The patient is a male aged 30–39, the leg is involved, close-up view.
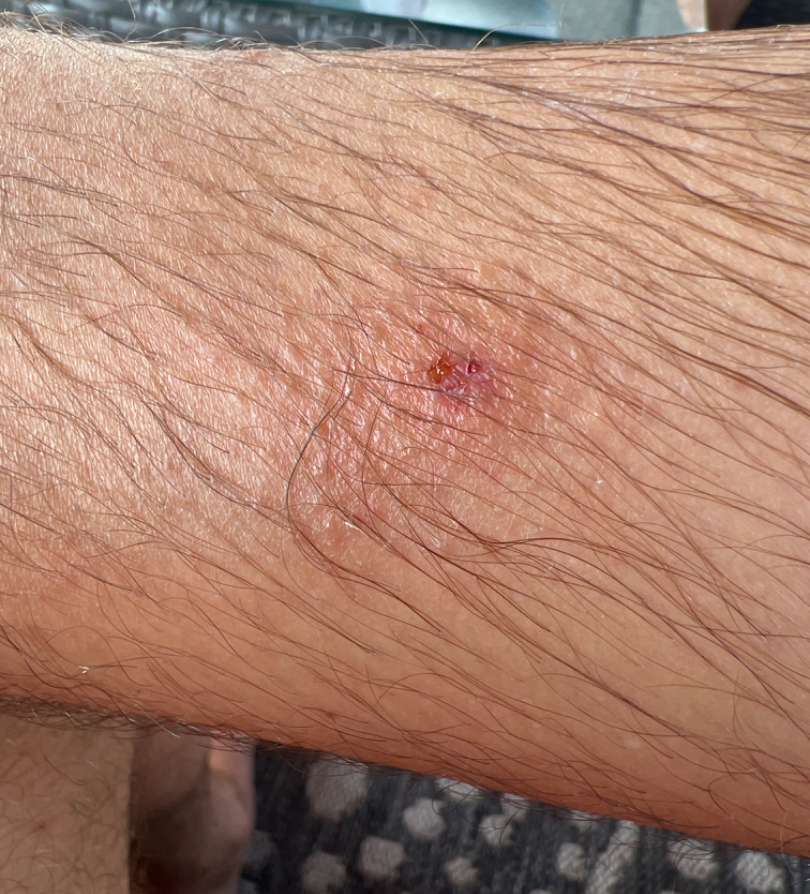Three independent reviewers: favoring Insect Bite; also on the differential is Allergic Contact Dermatitis; a remote consideration is Localized skin infection; less probable is Infected eczema.